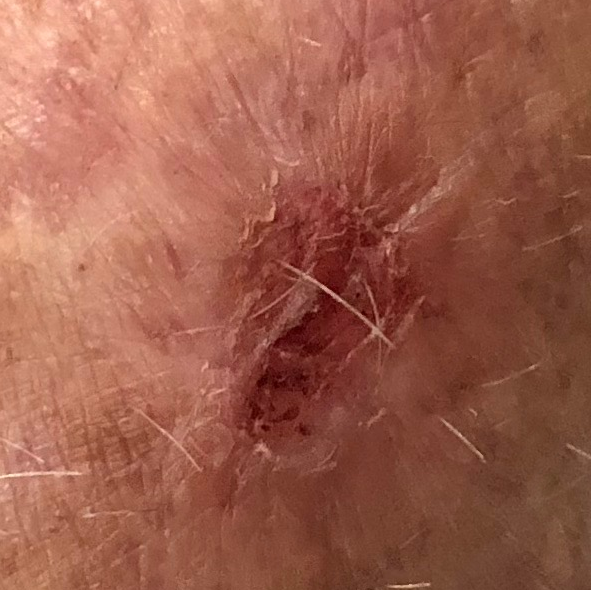Clinical context: Fitzpatrick II. The chart notes prior skin cancer (patient or family). A male patient in their early 70s. A clinical photograph showing a skin lesion. The lesion involves a forearm. The lesion is roughly 13 by 10 mm. The patient reports that the lesion itches and has bled, but has not changed. Pathology: Biopsy-confirmed as a premalignant lesion — an actinic keratosis.